A dermoscopic image of a skin lesion; acquired for a research image collection, with no referral diagnosis; the patient describes having a moderate number of moles; the patient reports a personal history of skin cancer, a personal history of cancer, no sunbed use, and no prior organ transplant: 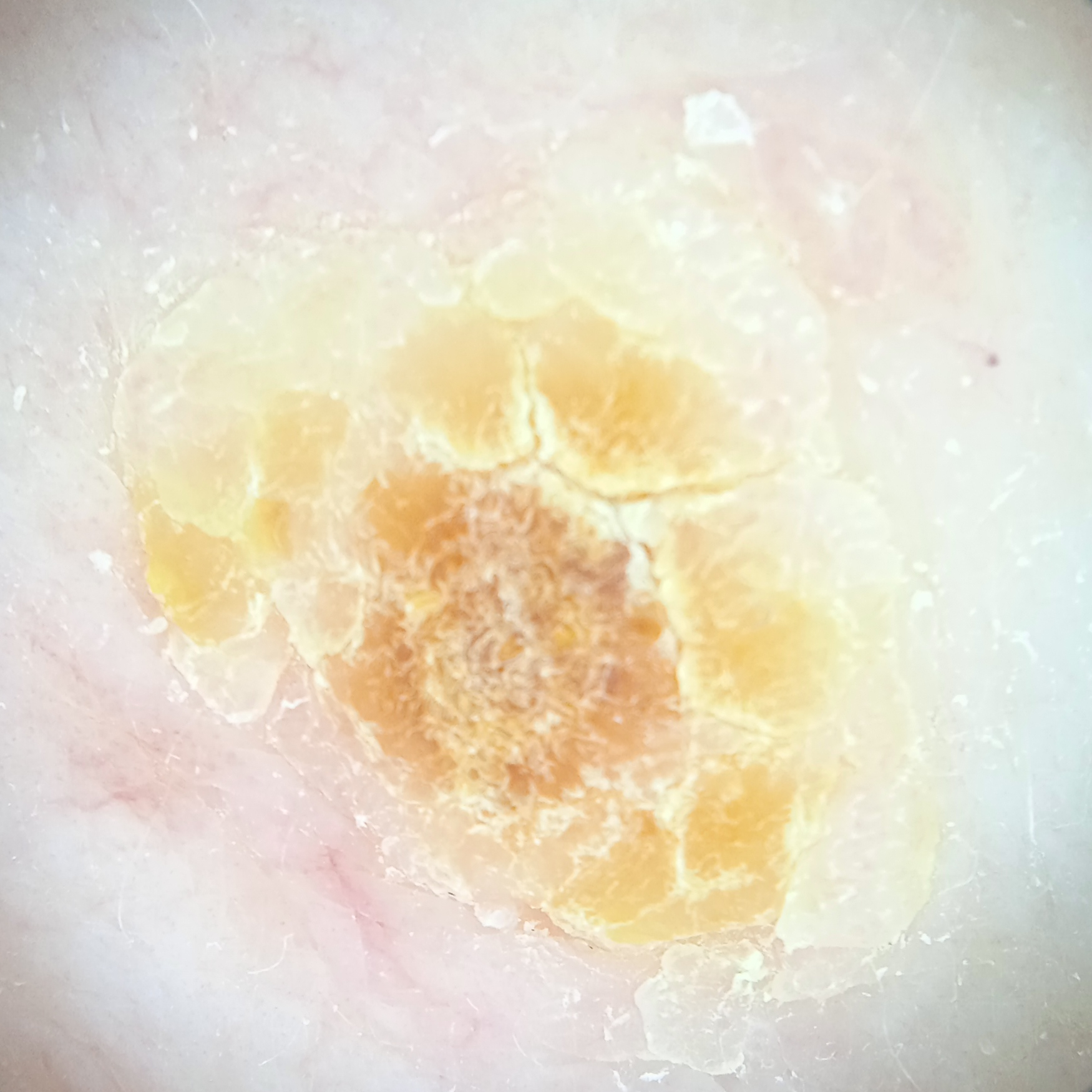site = the back; diameter = 11.1 mm; assessment = actinic keratosis (dermatologist consensus).